This is a close-up image; male patient, age 18–29; the leg and arm are involved.
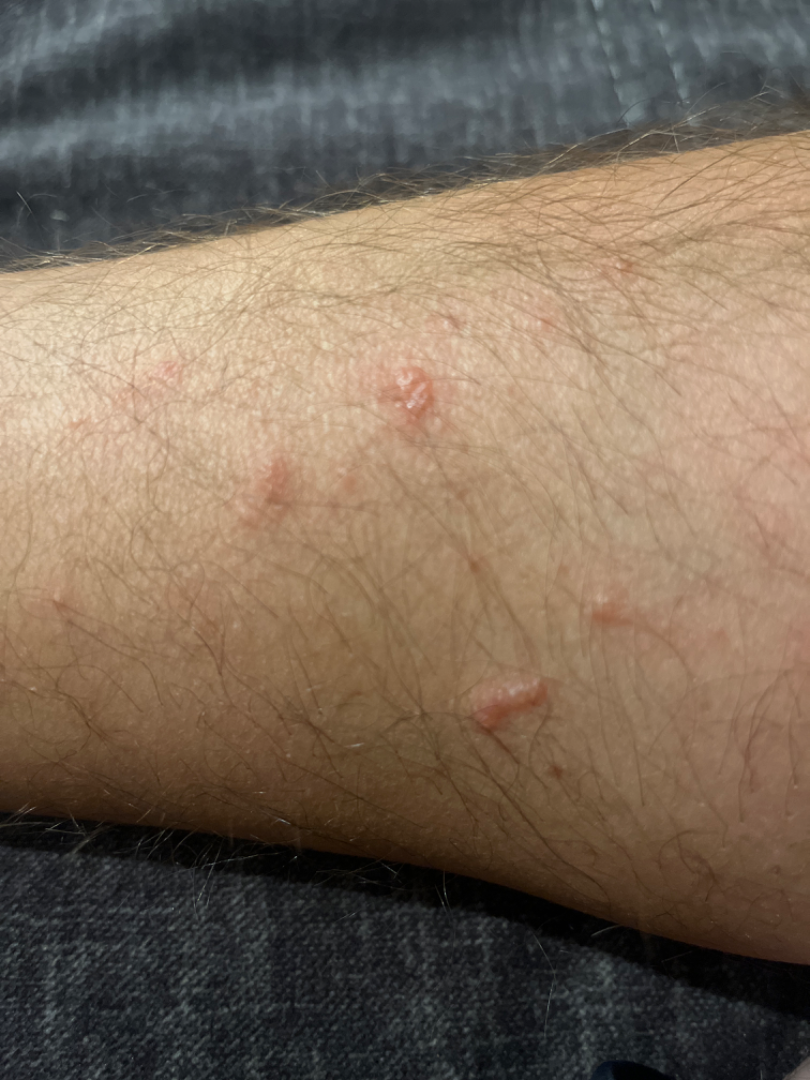Most consistent with Contact dermatitis caused by Rhus diversiloba.